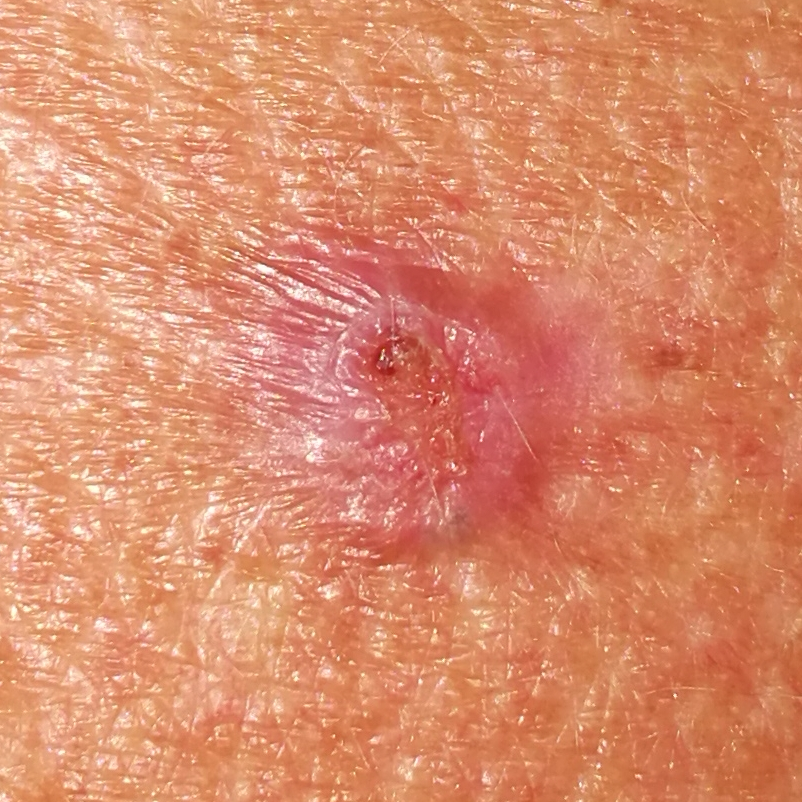Q: Any relevant history?
A: pesticide exposure, prior skin cancer (patient or family), no prior malignancy (patient or family), no tobacco use
Q: Patient demographics?
A: male, age 50
Q: What kind of image is this?
A: clinical photograph
Q: Where on the body is the lesion?
A: the back
Q: What are the lesion's dimensions?
A: 8x7 mm
Q: What is the diagnosis?
A: basal cell carcinoma (biopsy-proven)